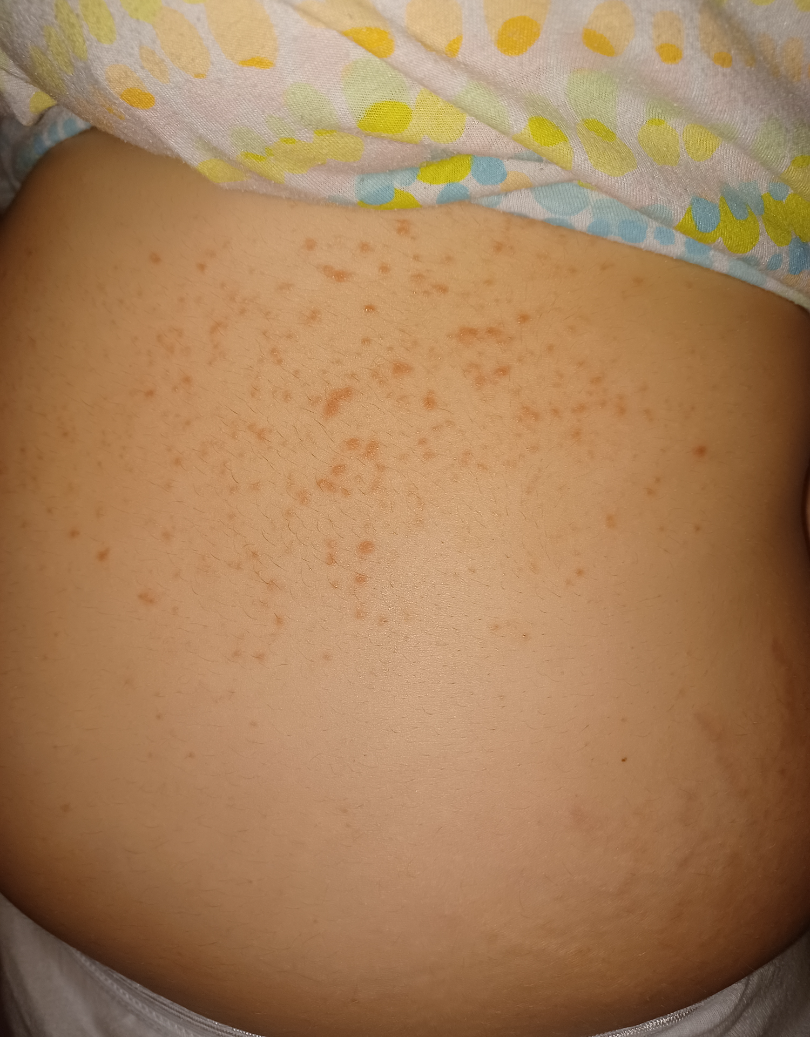Patient information: The subject is female. The patient considered this a rash. Located on the front of the torso. The condition has been present for one to four weeks. The contributor reports the lesion is raised or bumpy. Symptoms reported: bothersome appearance and darkening. This is a close-up image. Review: Three dermatologists independently reviewed the case: the impression was split between Eczema and Grover's disease; less likely is Miliaria; a more distant consideration is Folliculitis.